A dermatoscopic image of a skin lesion, a female patient aged 43 to 47: 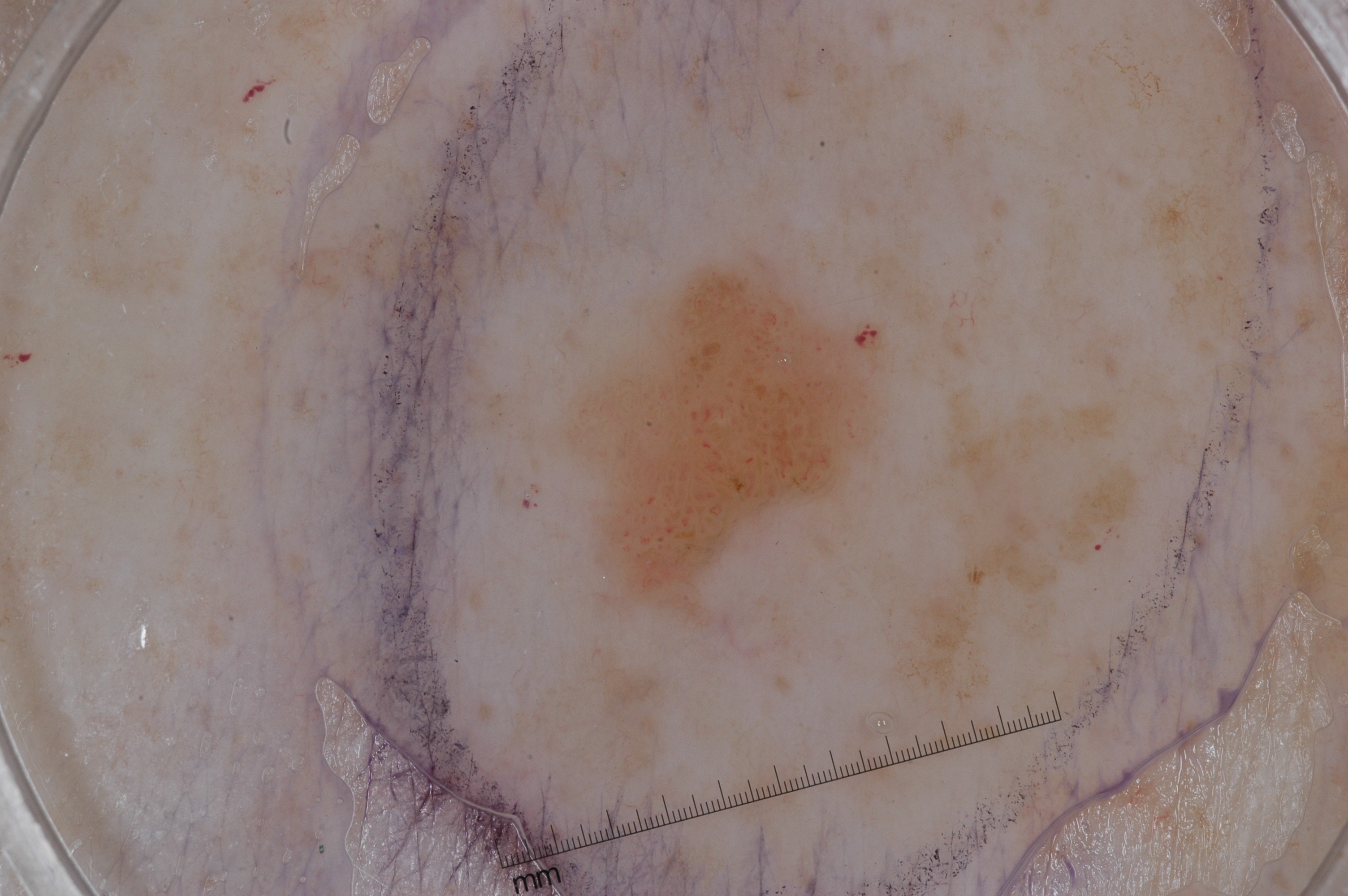absent dermoscopic findings = negative network, streaks, pigment network, and milia-like cysts; bounding box = (569, 259, 874, 602); lesion size = ~6% of the field; diagnostic label = a seborrheic keratosis.